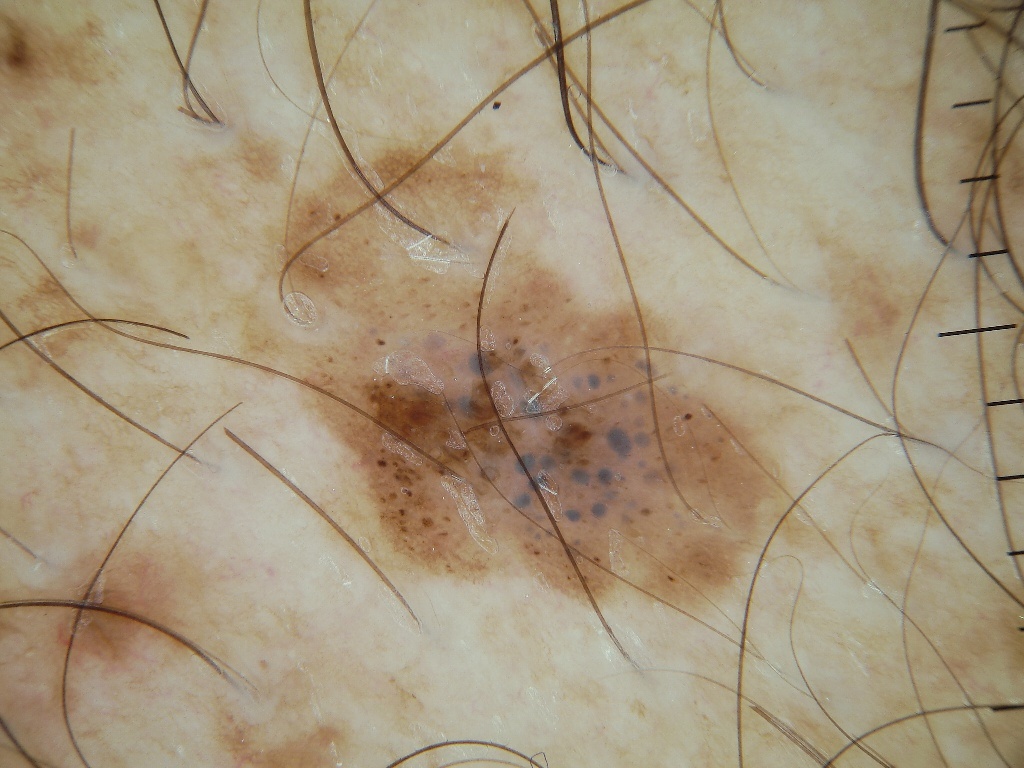Image and clinical context:
A dermoscopic close-up of a skin lesion. A moderately sized lesion. Lesion location: bbox(233, 117, 788, 609). Dermoscopically, the lesion shows globules.
Impression:
Clinically diagnosed as a benign skin lesion.